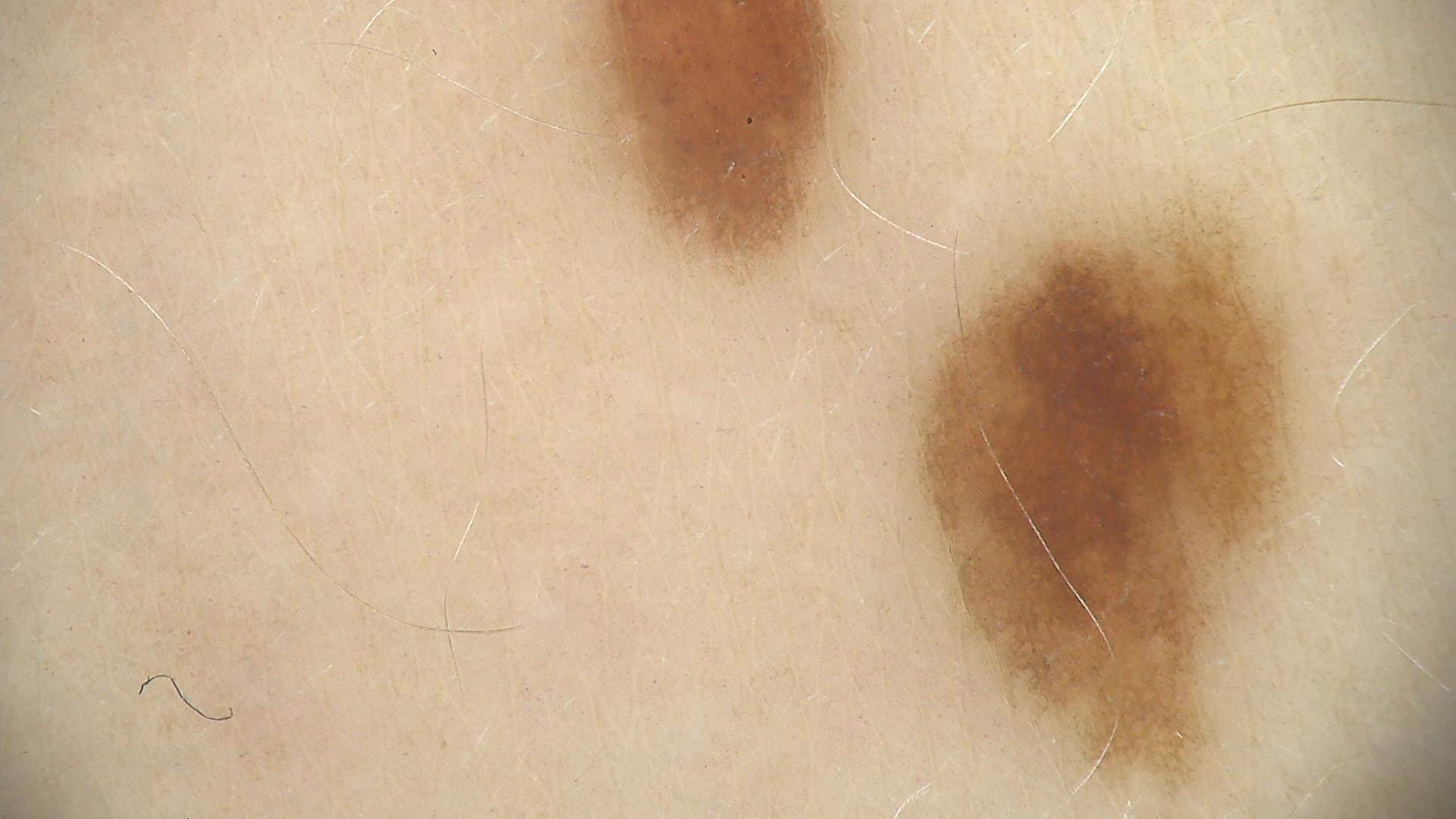{
  "image": "dermatoscopy",
  "diagnosis": {
    "name": "dysplastic junctional nevus",
    "code": "jd",
    "malignancy": "benign",
    "super_class": "melanocytic",
    "confirmation": "expert consensus"
  }
}